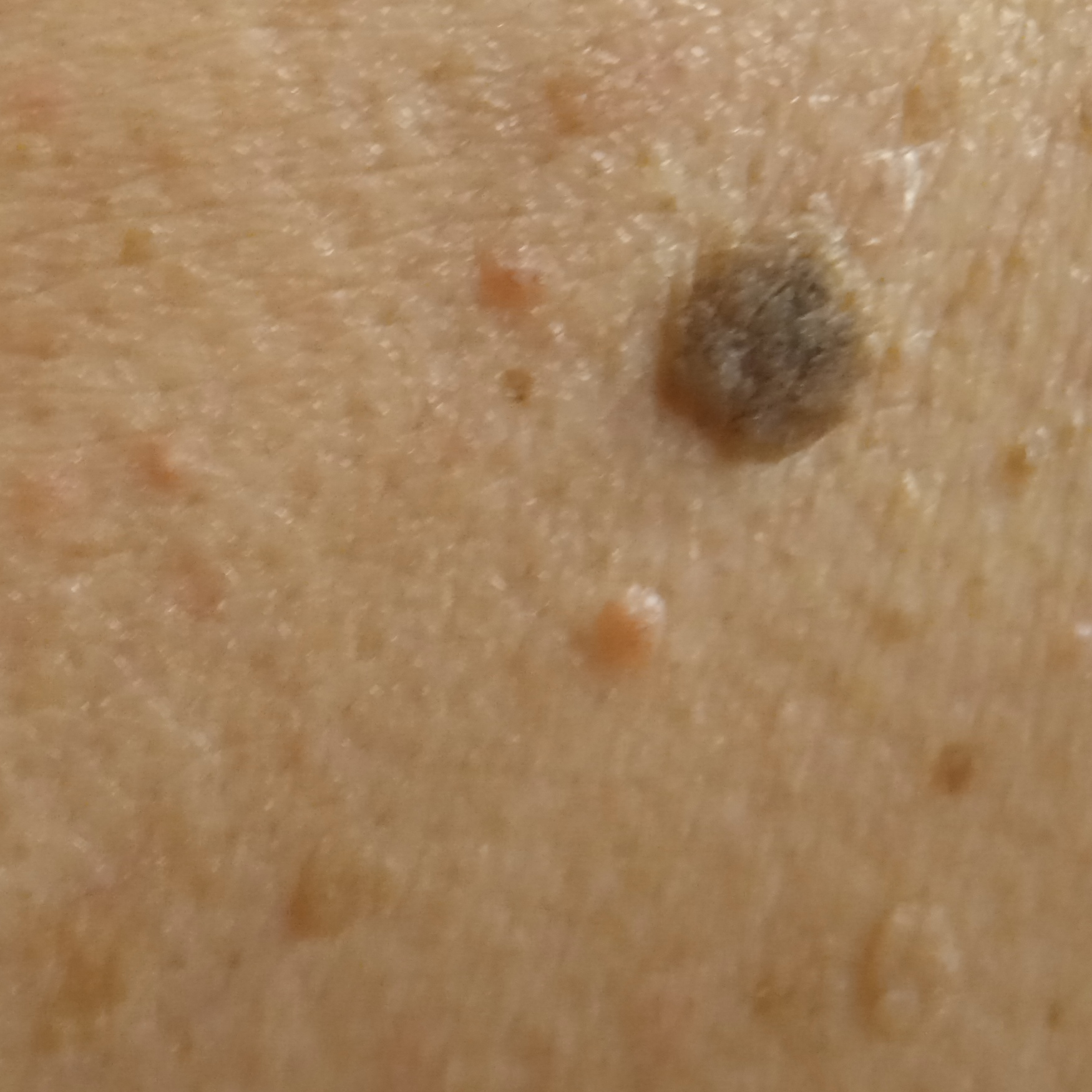{"diagnosis": {"name": "seborrheic keratosis", "malignancy": "benign"}}